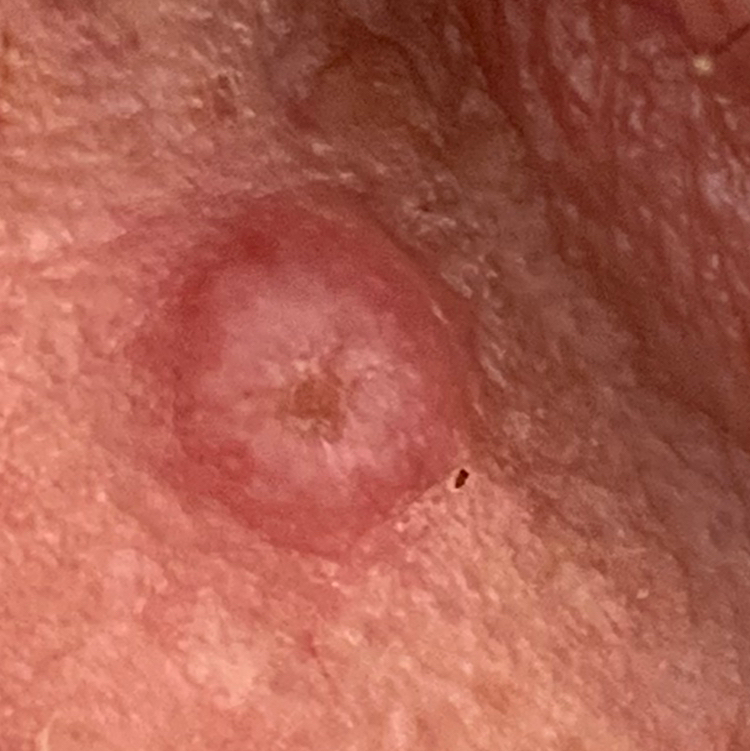image: clinical photograph
risk_factors:
  negative:
    - pesticide exposure
skin_type: II
patient:
  age: 84
  gender: female
lesion_location: the nose
lesion_size:
  diameter_1_mm: 7.0
  diameter_2_mm: 6.0
symptoms:
  present:
    - elevation
  absent:
    - growth
    - bleeding
diagnosis:
  name: squamous cell carcinoma
  code: SCC
  malignancy: malignant
  confirmation: histopathology